By self-report, a personal history of skin cancer and a personal history of cancer; a dermoscopy image of a skin lesion; a female patient age 75; imaged for a research study, with no referral diagnosis recorded: 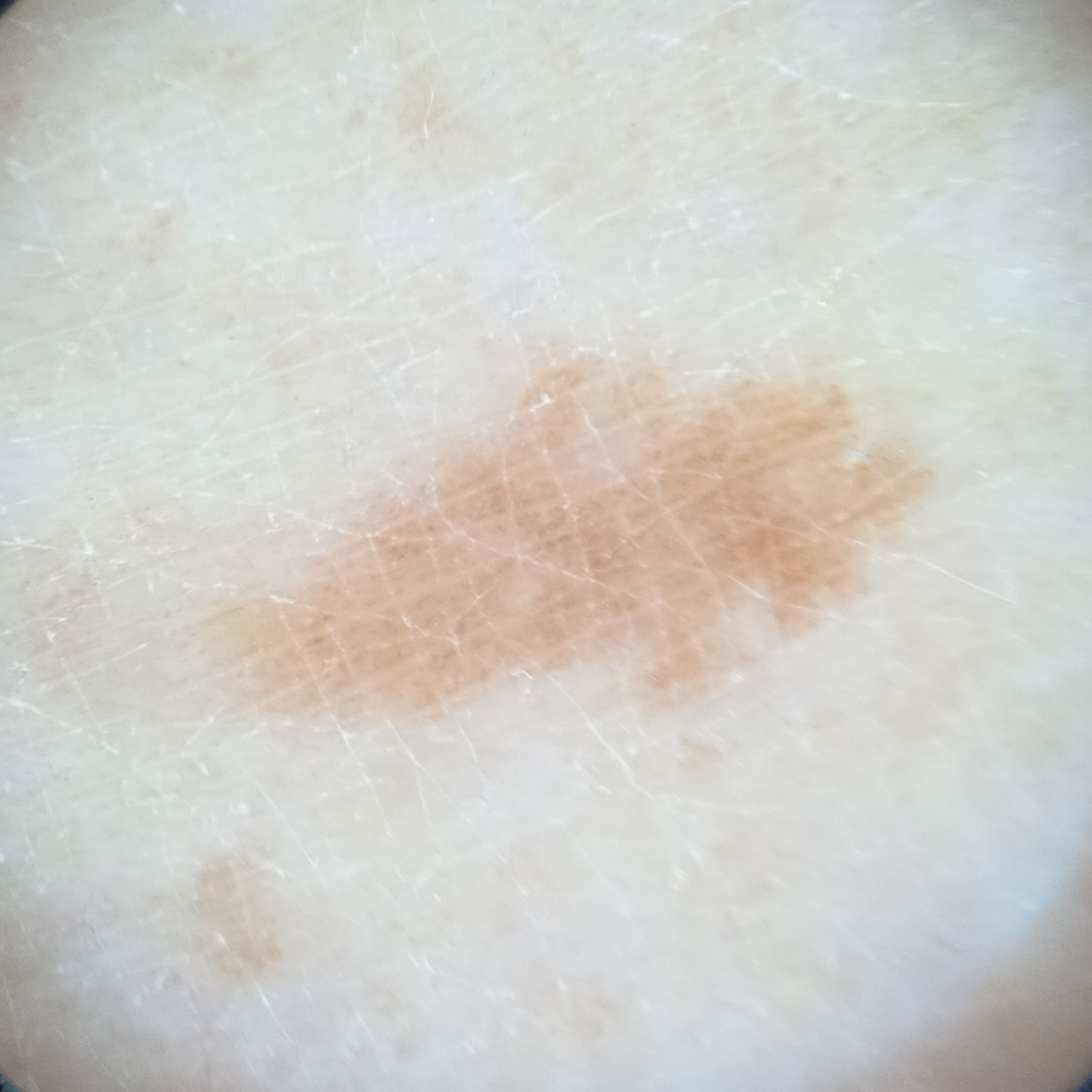  lesion_location: a leg
  lesion_size:
    diameter_mm: 8.2
  diagnosis:
    name: melanocytic nevus
    malignancy: benign